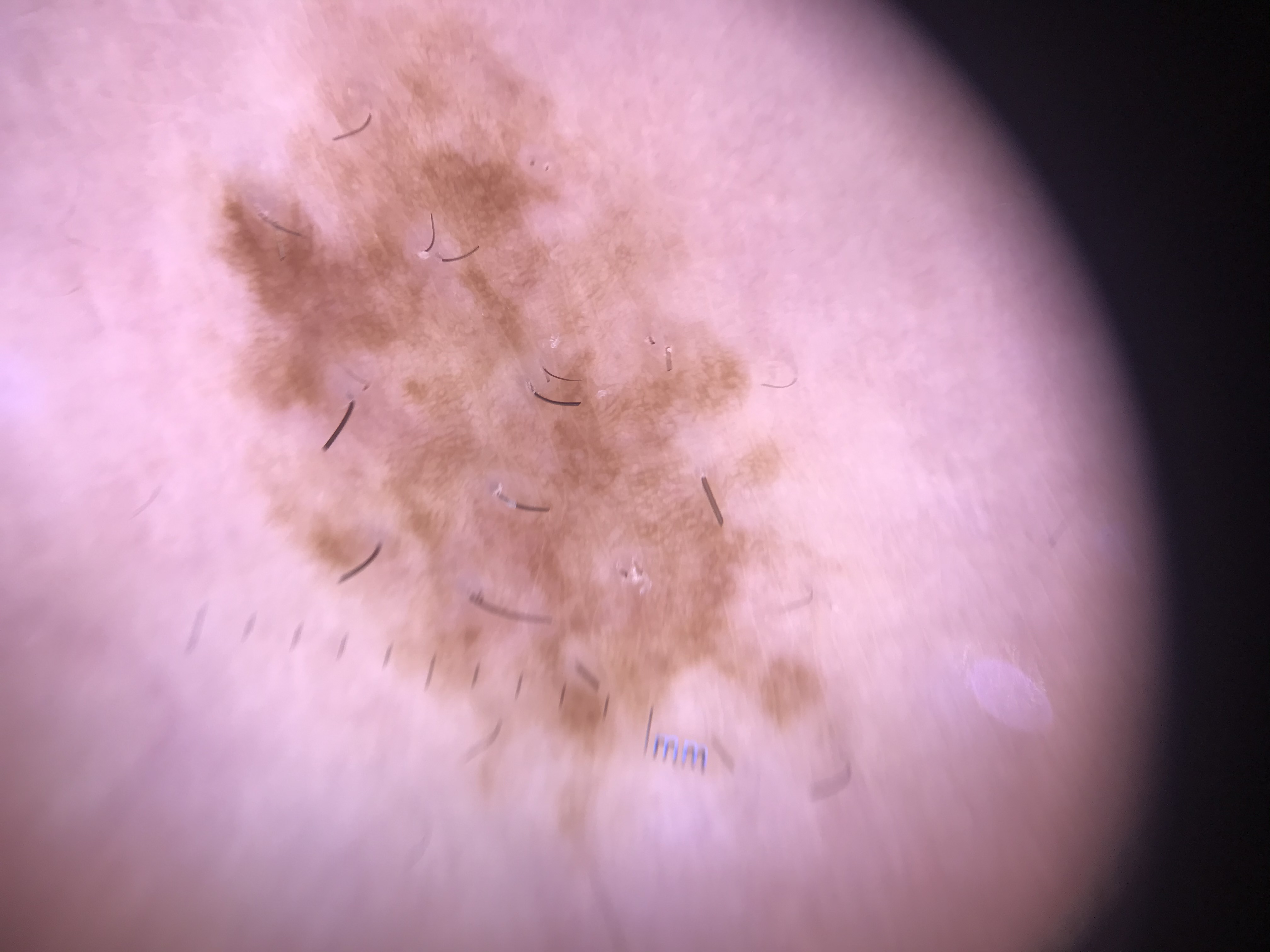modality: dermatoscopy | classification: banal | assessment: congenital compound nevus (expert consensus).